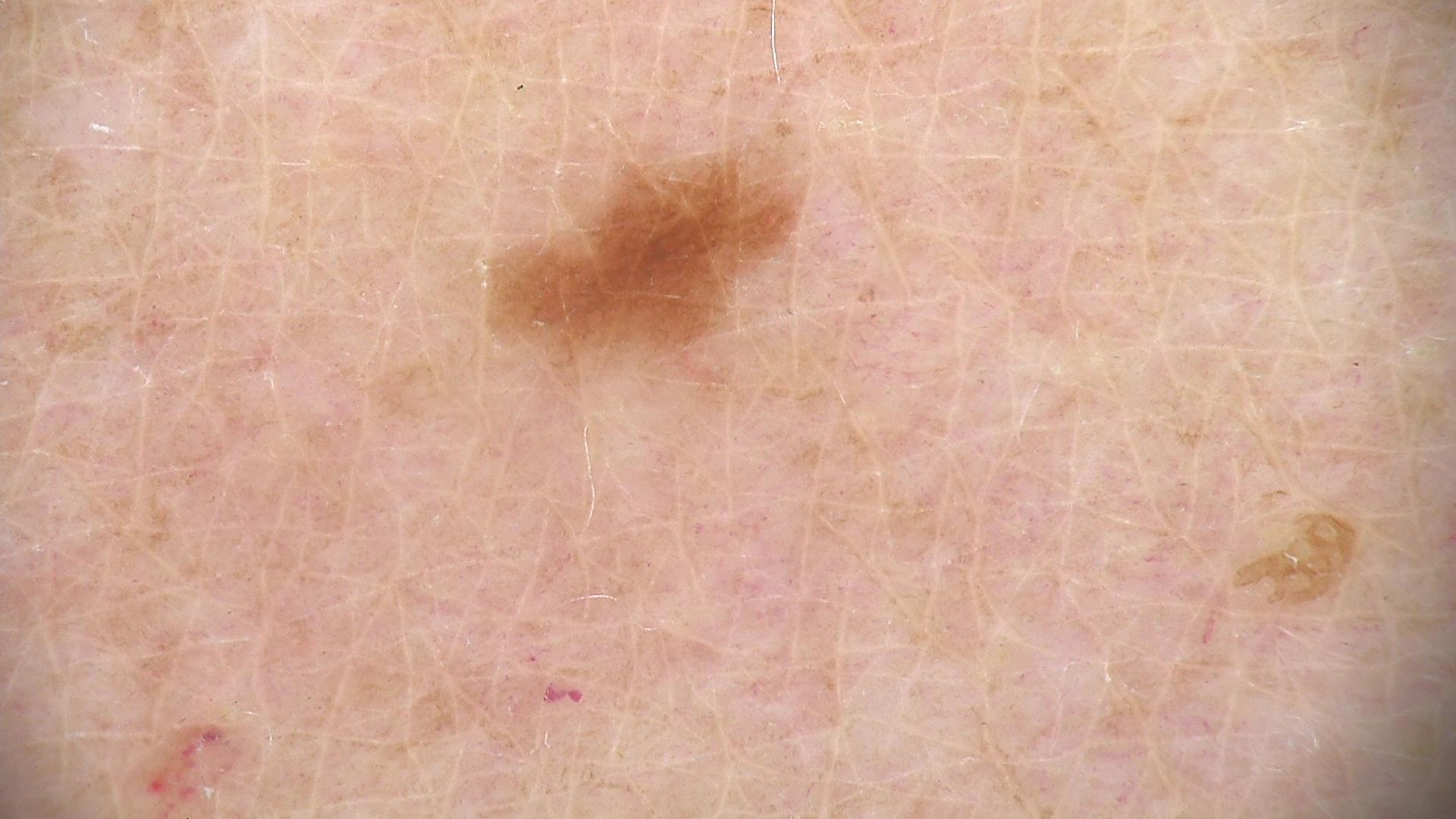The architecture is that of a banal lesion.
The diagnosis was a junctional nevus.